A dermatoscopic image of a skin lesion.
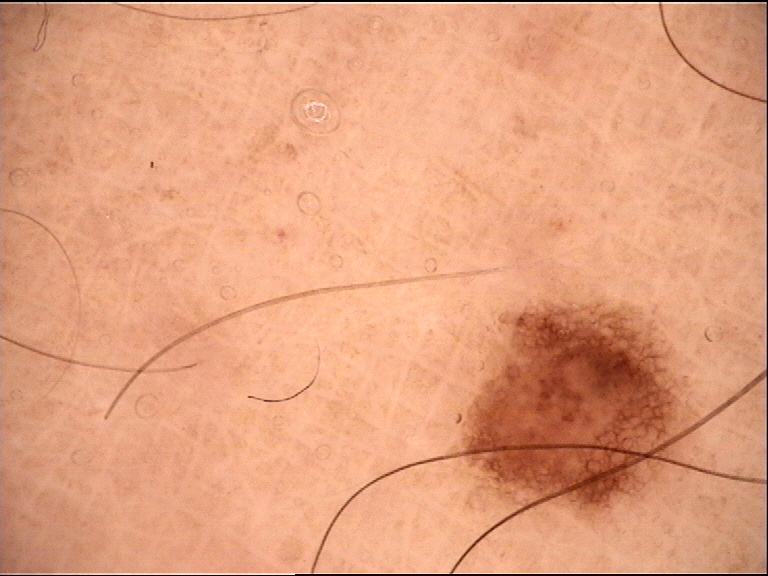Impression:
Classified as a benign lesion — a dysplastic junctional nevus.